A wide-field clinical photograph of a skin lesion. A male subject aged 83 or over. Recorded as skin type III.
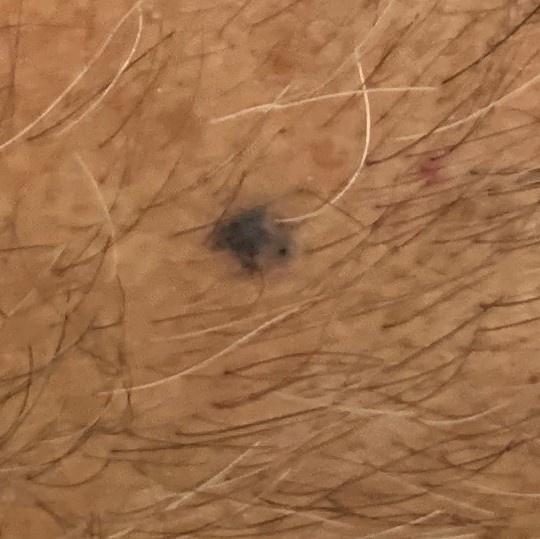diagnosis: Basal cell carcinoma (biopsy-proven)